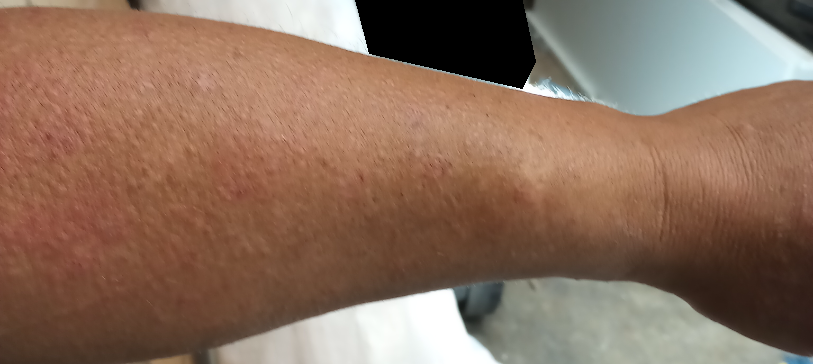The contributor is a male aged 40–49. The photograph was taken at a distance. Located on the arm, front of the torso and leg.